The lesion involves the back of the torso and front of the torso. This is a close-up image. Male subject, age 30–39 — 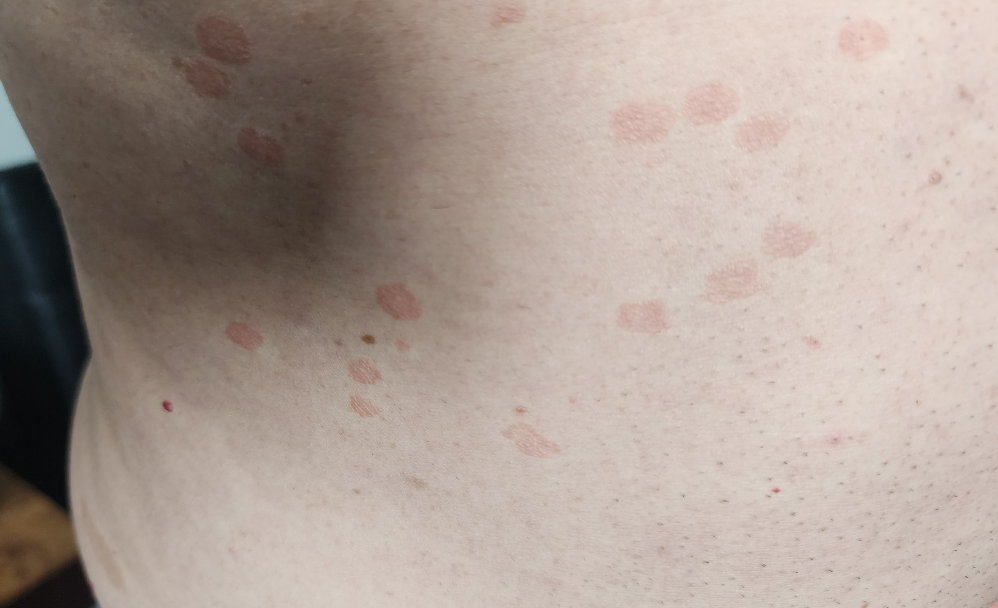| key | value |
|---|---|
| duration | one to three months |
| associated systemic symptoms | none reported |
| patient-reported symptoms | none reported |
| described texture | flat |
| differential diagnosis | reviewed remotely by three dermatologists: most likely Psoriasis; less likely is Pityriasis rosea; a more distant consideration is Tinea Versicolor; less probable is Parapsoriasis; lower on the differential is Seborrheic Dermatitis |